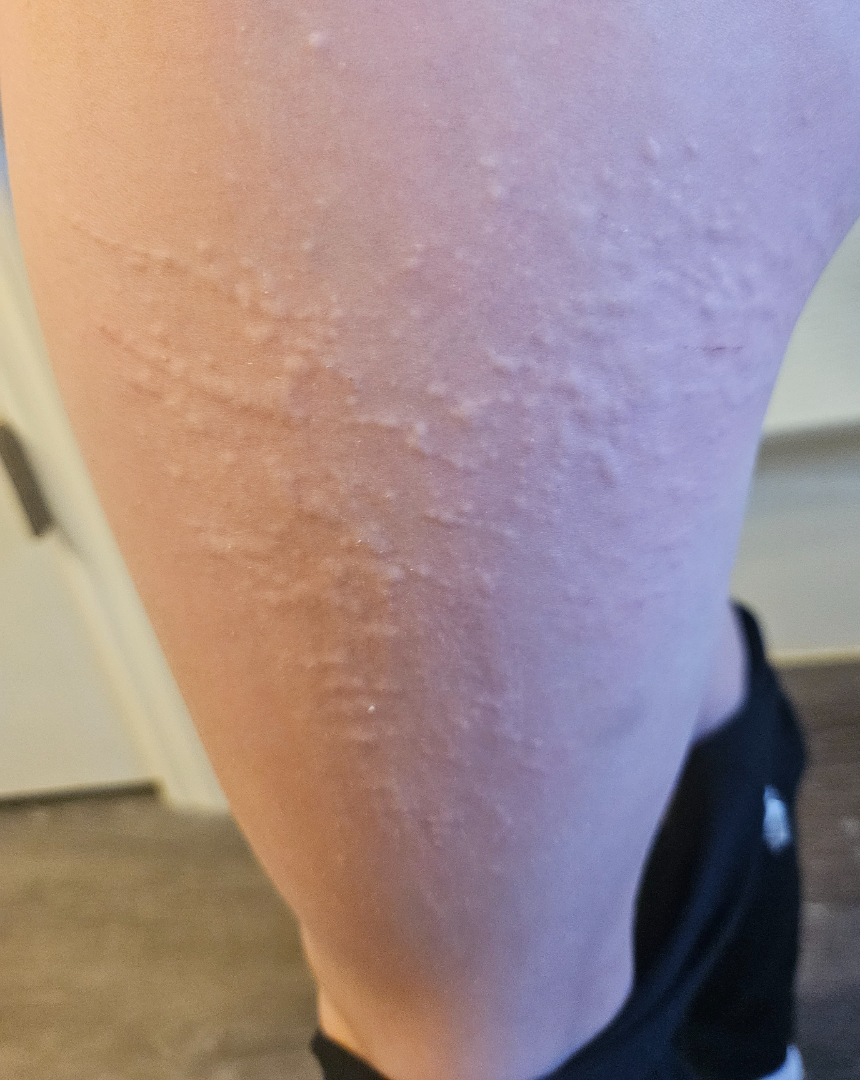texture: raised or bumpy
shot_type: close-up
skin_tone:
  monk_skin_tone:
    - 1
    - 2
body_site: leg
systemic_symptoms: none reported
symptoms: itching
duration: less than one week
patient: female, age 18–29
differential:
  leading:
    - Urticaria
  considered:
    - Lichen nitidus
    - Allergic Contact Dermatitis